Close-up view, the lesion involves the arm:
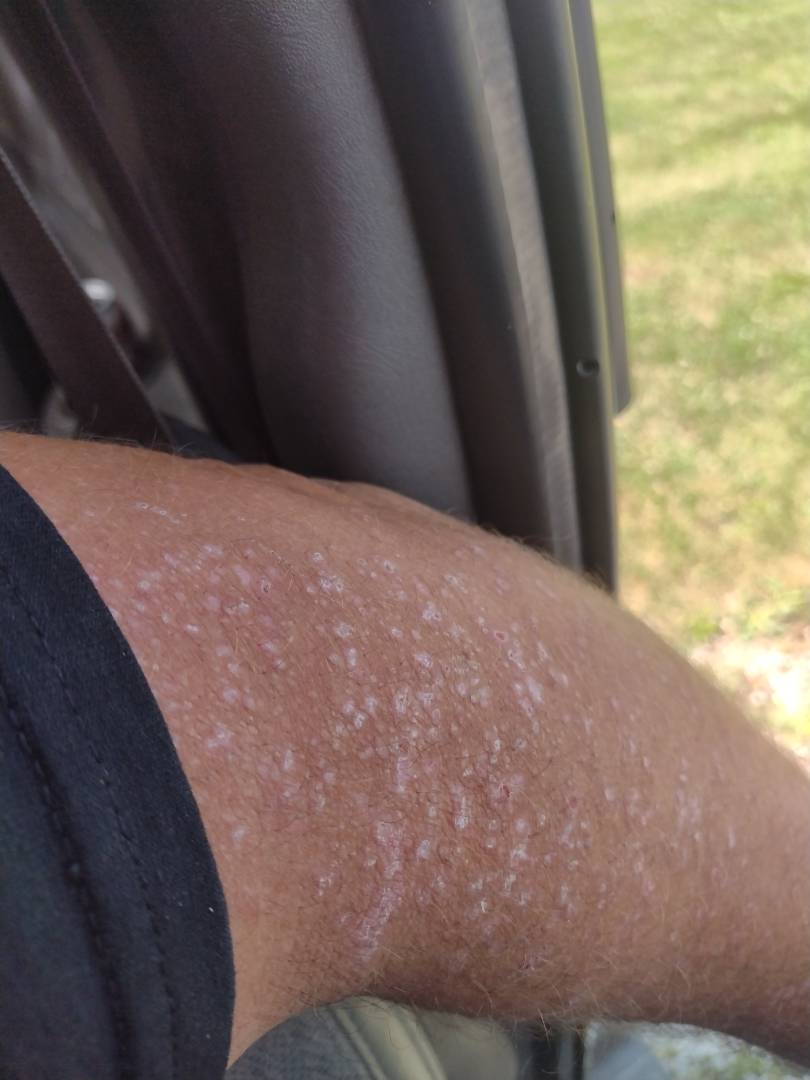| field | value |
|---|---|
| impression | the favored diagnosis is Psoriasis; with consideration of Drug Rash |